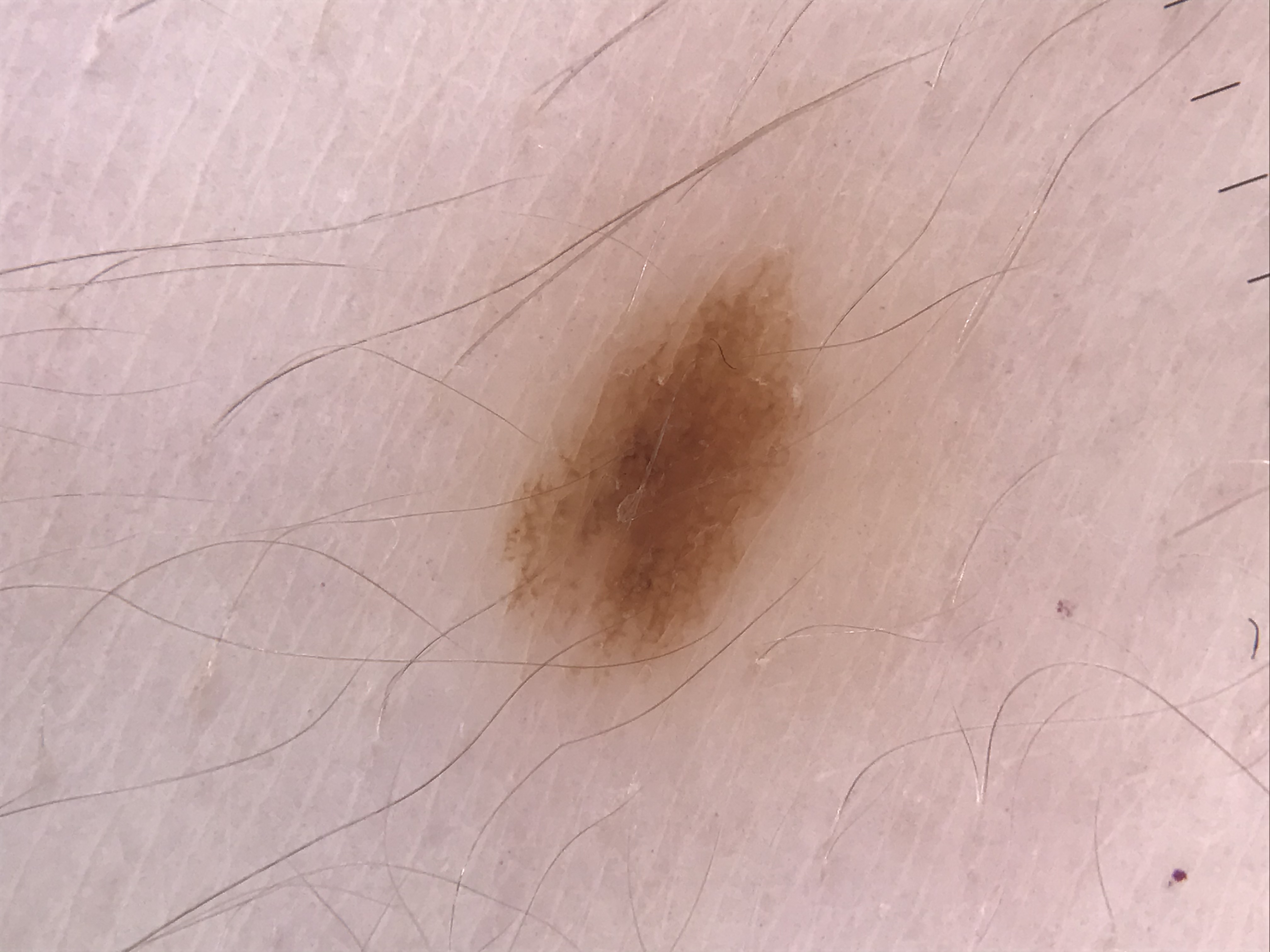Diagnosed as a dysplastic junctional nevus.